The patient describes having a moderate number of moles; a dermatoscopic image of a skin lesion; the patient says their skin reddens painfully with sun exposure; a female patient 81 years old; imaged for a research study, with no referral diagnosis recorded: 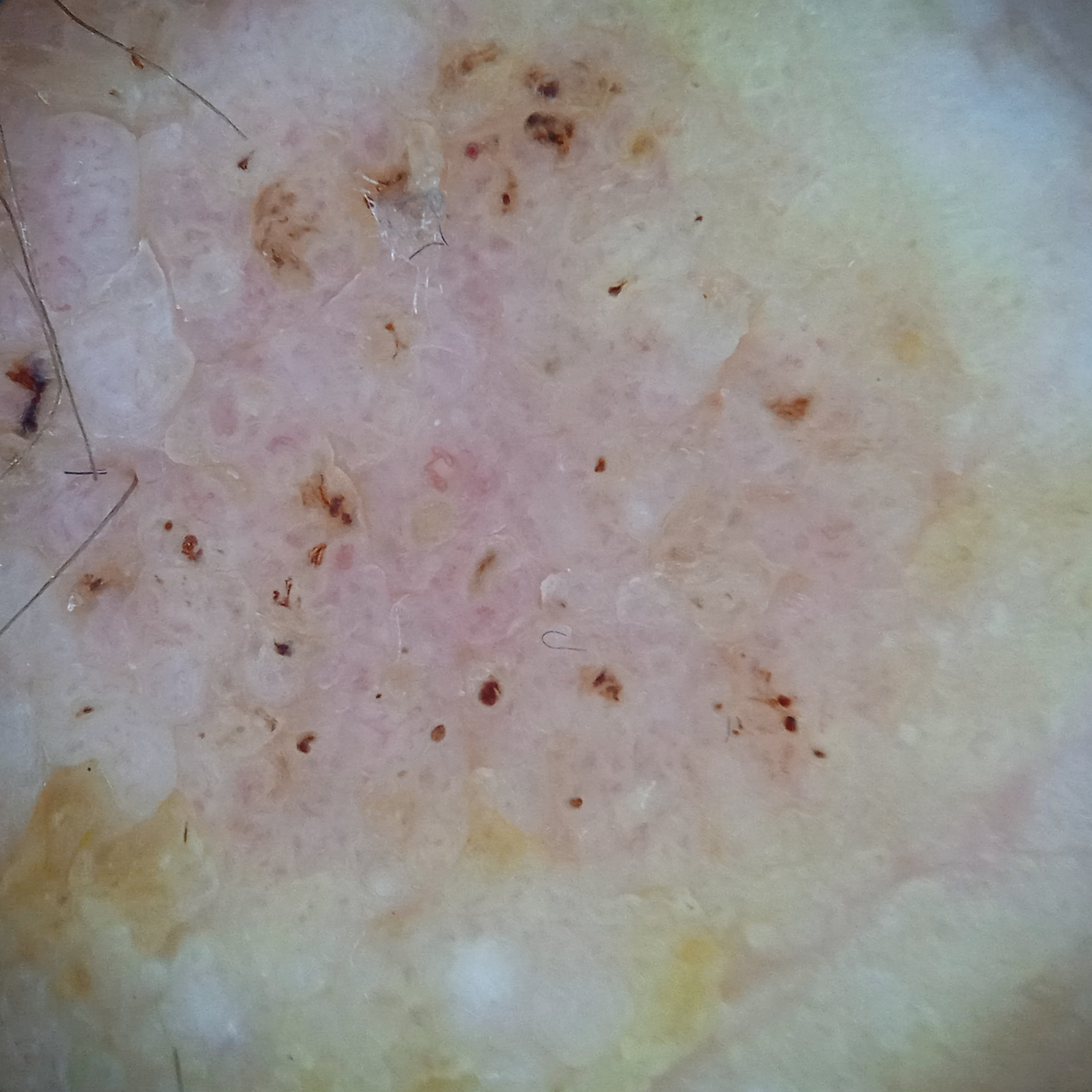body site=the face; size=36.6 mm; diagnostic label=seborrheic keratosis (dermatologist consensus).